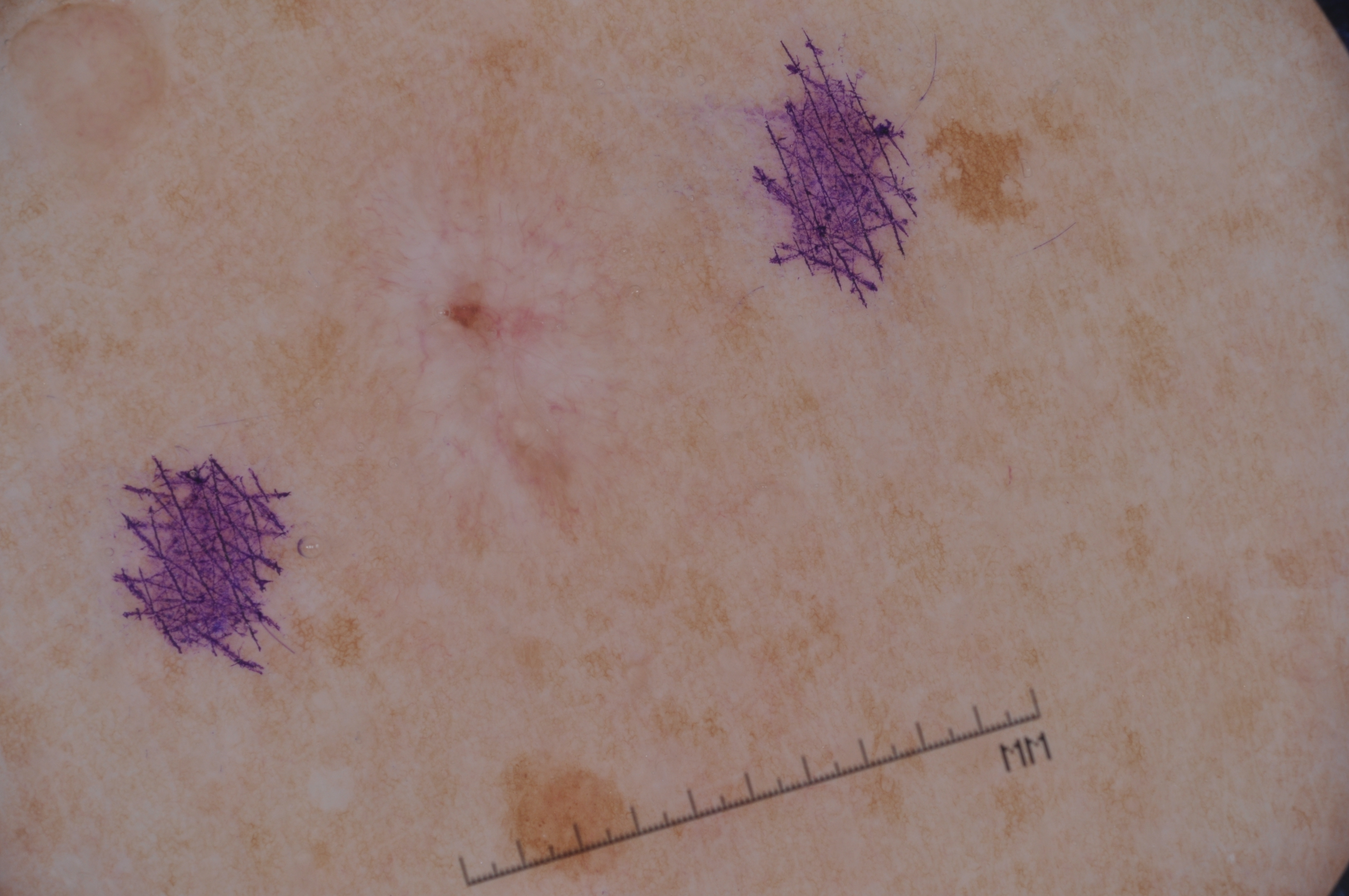Findings:
* modality — dermoscopic image
* subject — female, aged around 40
* lesion location — [312, 111, 645, 585]
* dermoscopic features assessed but absent — milia-like cysts, pigment network, streaks, and negative network
* lesion extent — moderate
* diagnosis — a melanocytic nevus